A skin lesion imaged with a dermatoscope. The patient says their skin reddens with sun exposure. On a questionnaire the patient reported a personal history of skin cancer and a personal history of cancer. A moderate number of moles by the patient's own estimate:
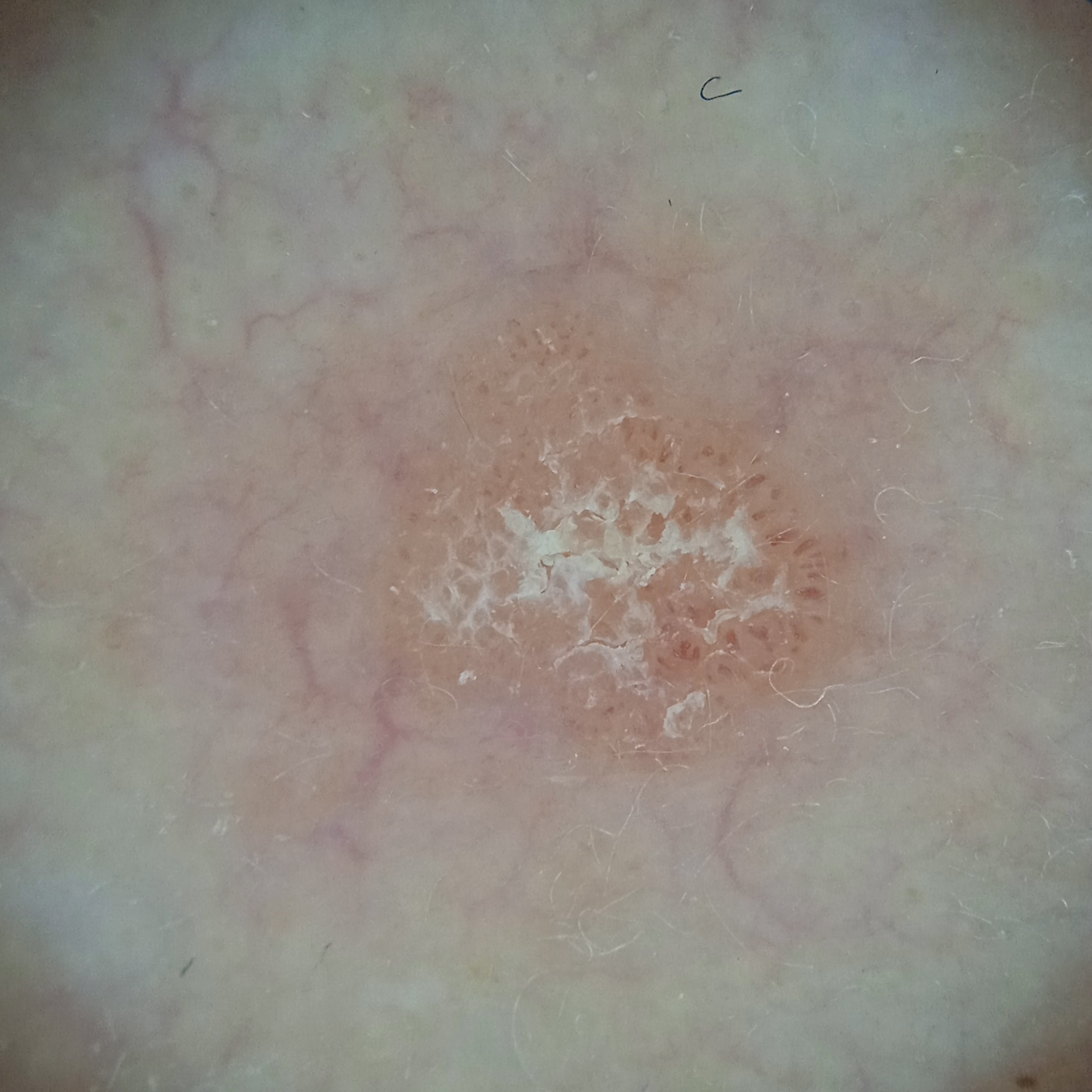site — the face; diagnosis — actinic keratosis (dermatologist consensus).